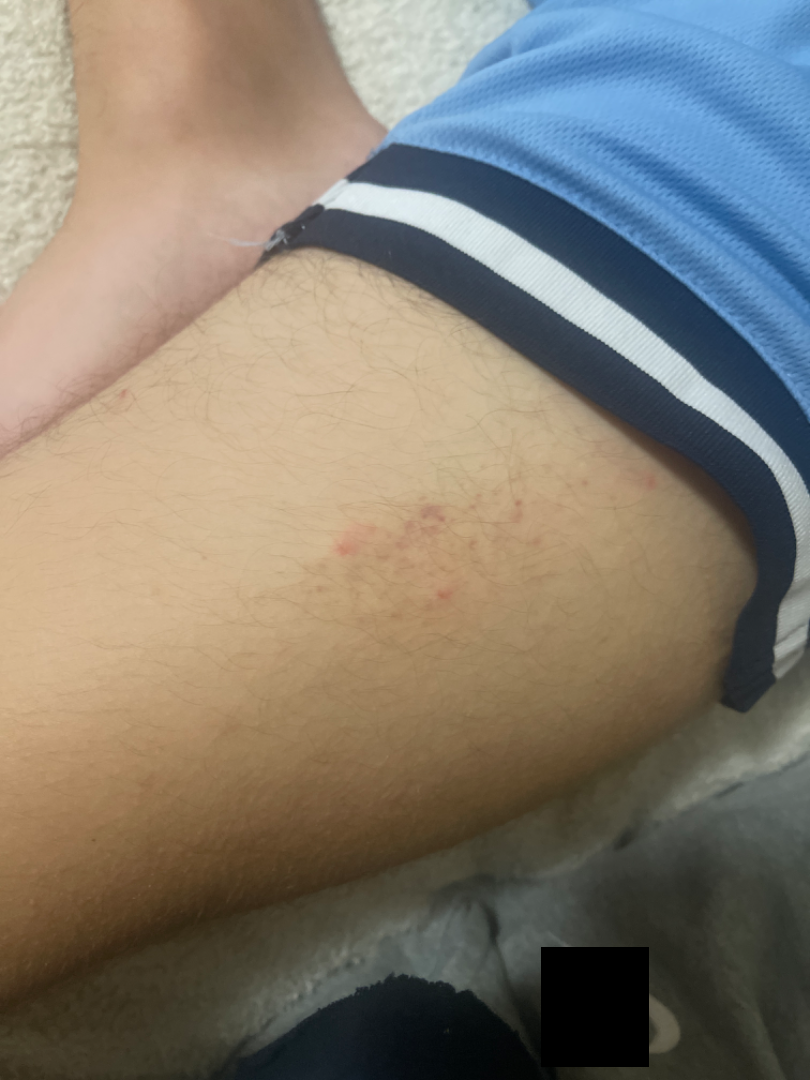No constitutional symptoms were reported. This image was taken at a distance. The patient described the issue as a rash. The lesion is associated with enlargement, pain, itching and burning. The lesion involves the leg. The patient notes the lesion is raised or bumpy. Skin tone: FST III; human graders estimated Monk Skin Tone 3 or 4 (two reviewer pools). Present for about one day. Reviewed remotely by one dermatologist: the differential includes Folliculitis, ecchymoses and Post-Inflammatory hyperpigmentation, with no clear leading consideration.